The leg is involved, close-up view.
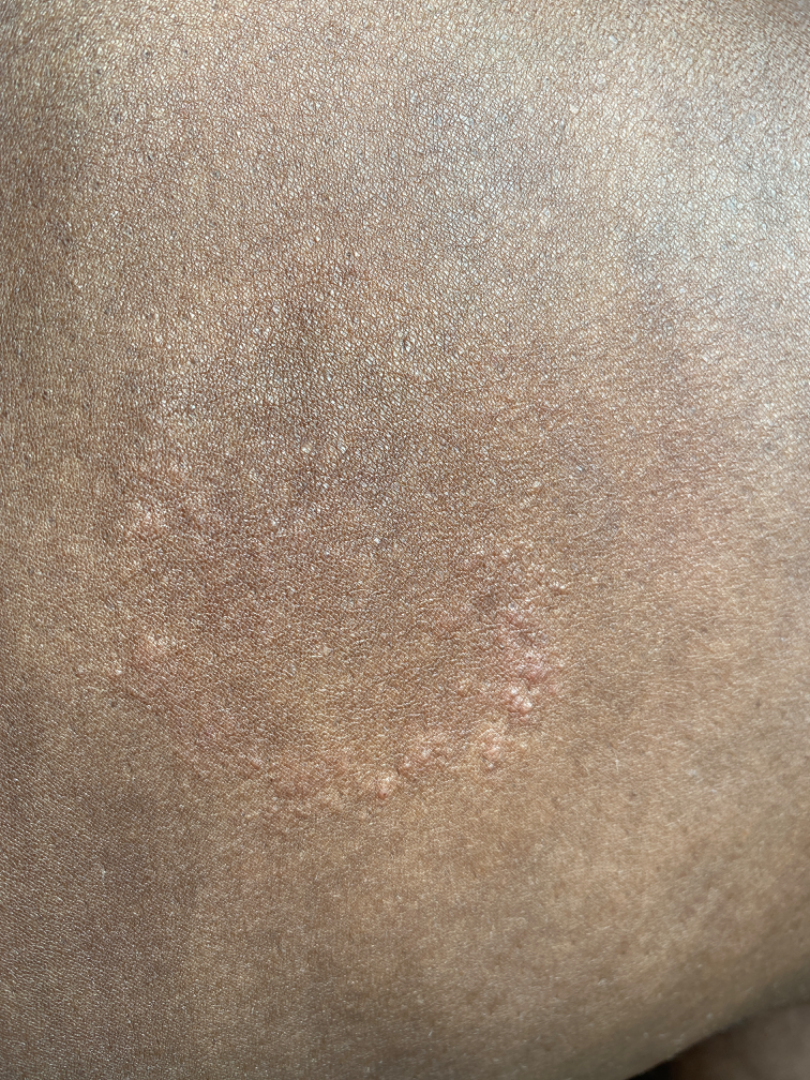| feature | finding |
|---|---|
| diagnostic considerations | most likely Tinea; an alternative is Lichen planus/lichenoid eruption; the differential also includes Eczema |